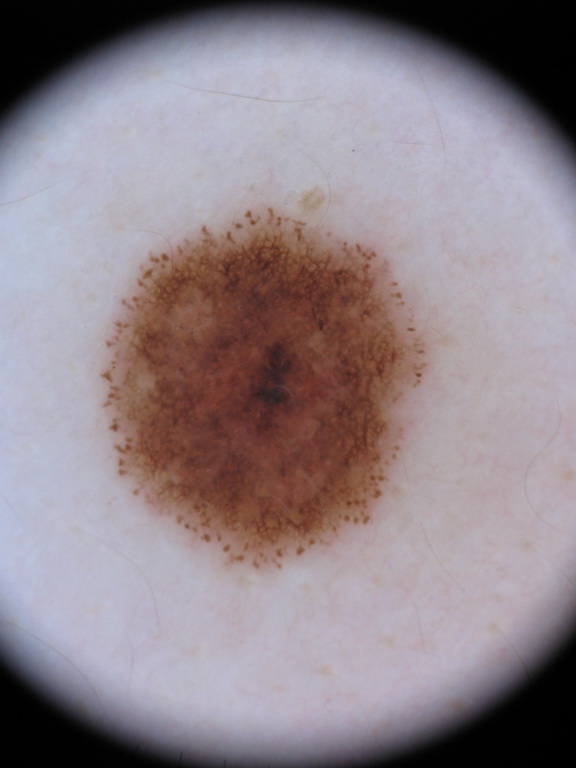Case summary:
A dermoscopic view of a skin lesion. The patient is a male aged 28 to 32. The dermoscopic pattern shows pigment network and globules. The lesion occupies roughly 19% of the field. The lesion occupies the region bbox=[102, 207, 429, 567].
Conclusion:
The lesion was assessed as a melanocytic nevus, a benign lesion.